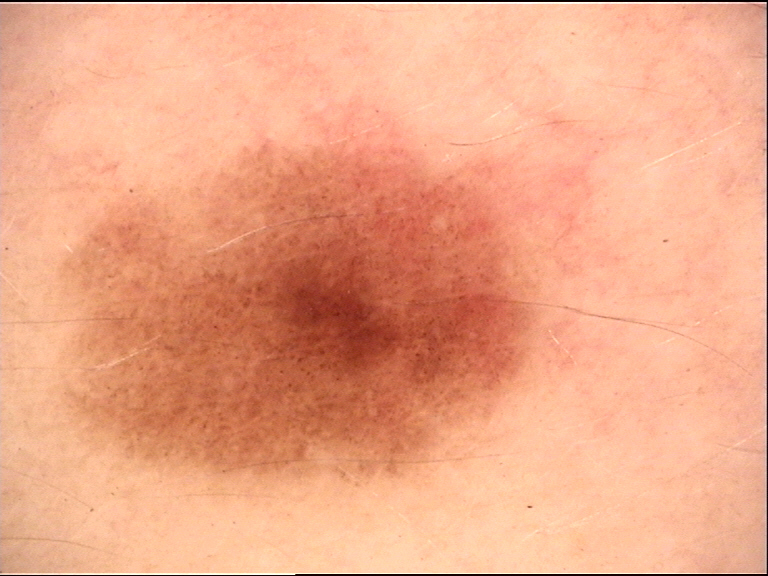Conclusion: Consistent with a benign lesion — a dysplastic junctional nevus.